Located on the arm and leg; symptoms reported: itching; this is a close-up image; the patient is 30–39, male; the patient described the issue as a rash; reported duration is less than one week: 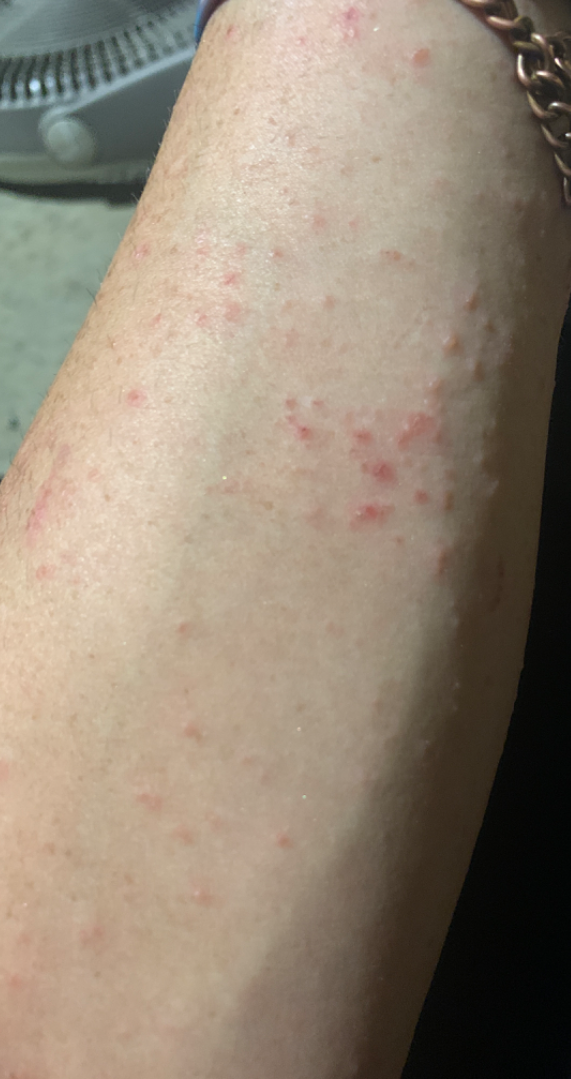Findings:
– assessment · favoring Eczema; with consideration of Allergic Contact Dermatitis; lower on the differential is Molluscum Contagiosum; less probable is Hypersensitivity; less likely is Irritant Contact Dermatitis